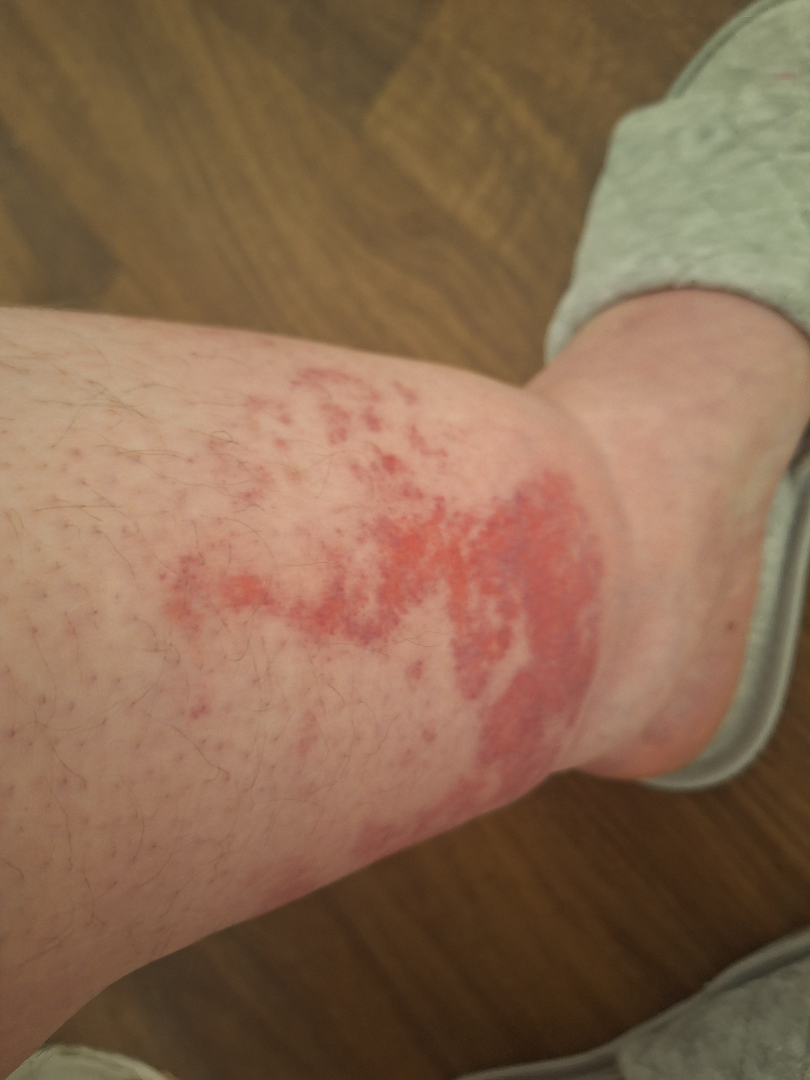<case>
<body_site>leg</body_site>
<patient>female, age 40–49</patient>
<shot_type>close-up</shot_type>
<differential>
  <leading>Venous Stasis Ulcer</leading>
</differential>
</case>